Texture is reported as raised or bumpy · the photograph is a close-up of the affected area · the patient notes the condition has been present for one to three months · symptoms reported: itching · the patient is 40–49, female · located on the arm · the patient considered this a rash · no constitutional symptoms were reported:
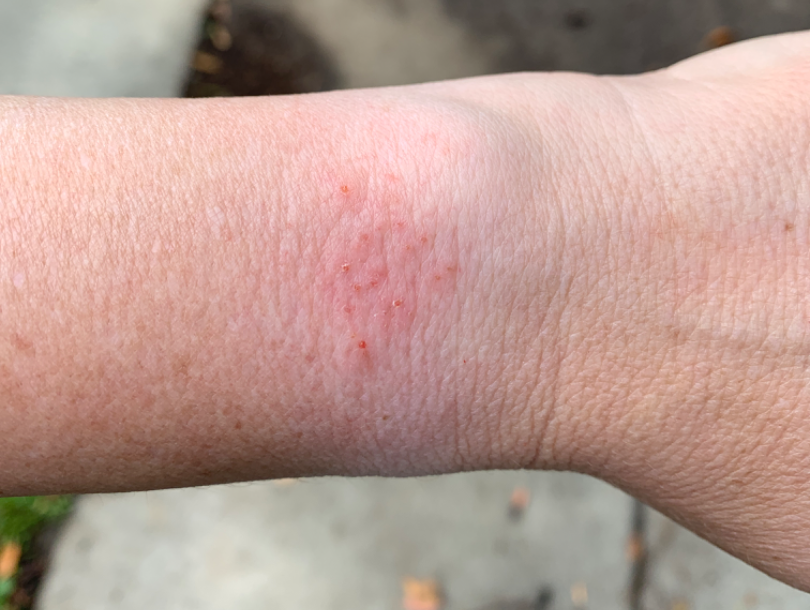Notes:
– impression: Insect Bite, Eczema and Allergic Contact Dermatitis were each considered, in no particular order